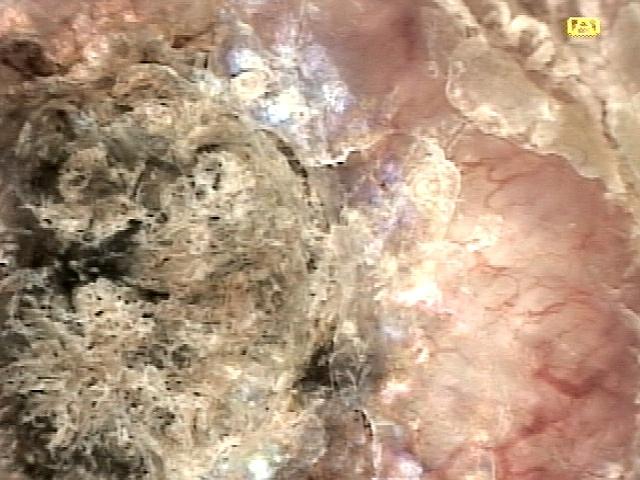A female subject aged around 75. A skin lesion imaged with contact-polarized dermoscopy. The lesion involves a lower extremity. Histopathological examination showed a squamous cell carcinoma.